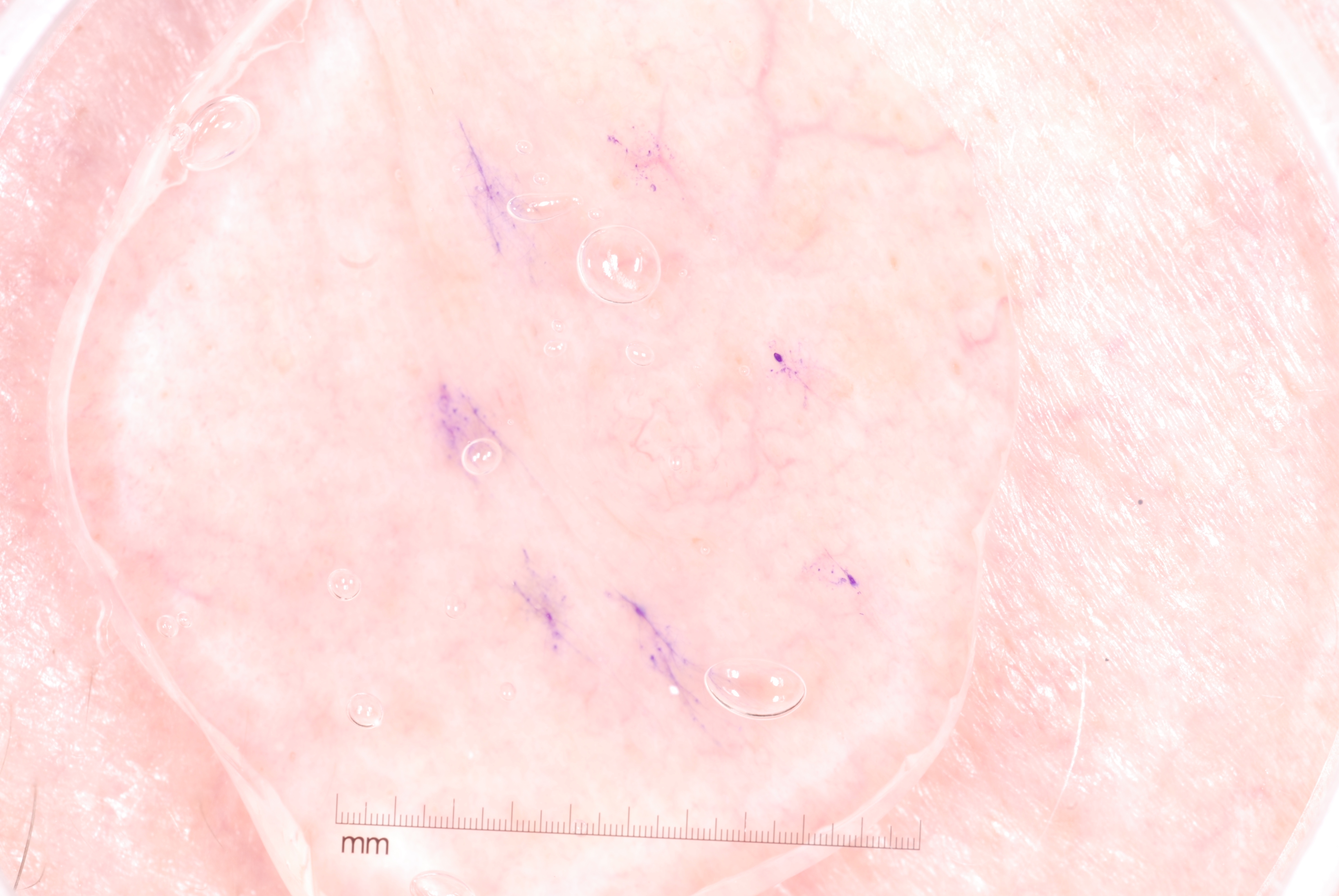Q: What are the patient's age and sex?
A: female, in their 60s
Q: What is the imaging modality?
A: dermoscopic image
Q: How large is the lesion within the image?
A: moderate
Q: What dermoscopic features are not present?
A: negative network, pigment network, streaks, and milia-like cysts
Q: What is the lesion's bounding box?
A: left=449, top=171, right=904, bottom=729
Q: What is this lesion?
A: a melanocytic nevus, a benign lesion